Dermoscopy of a skin lesion:
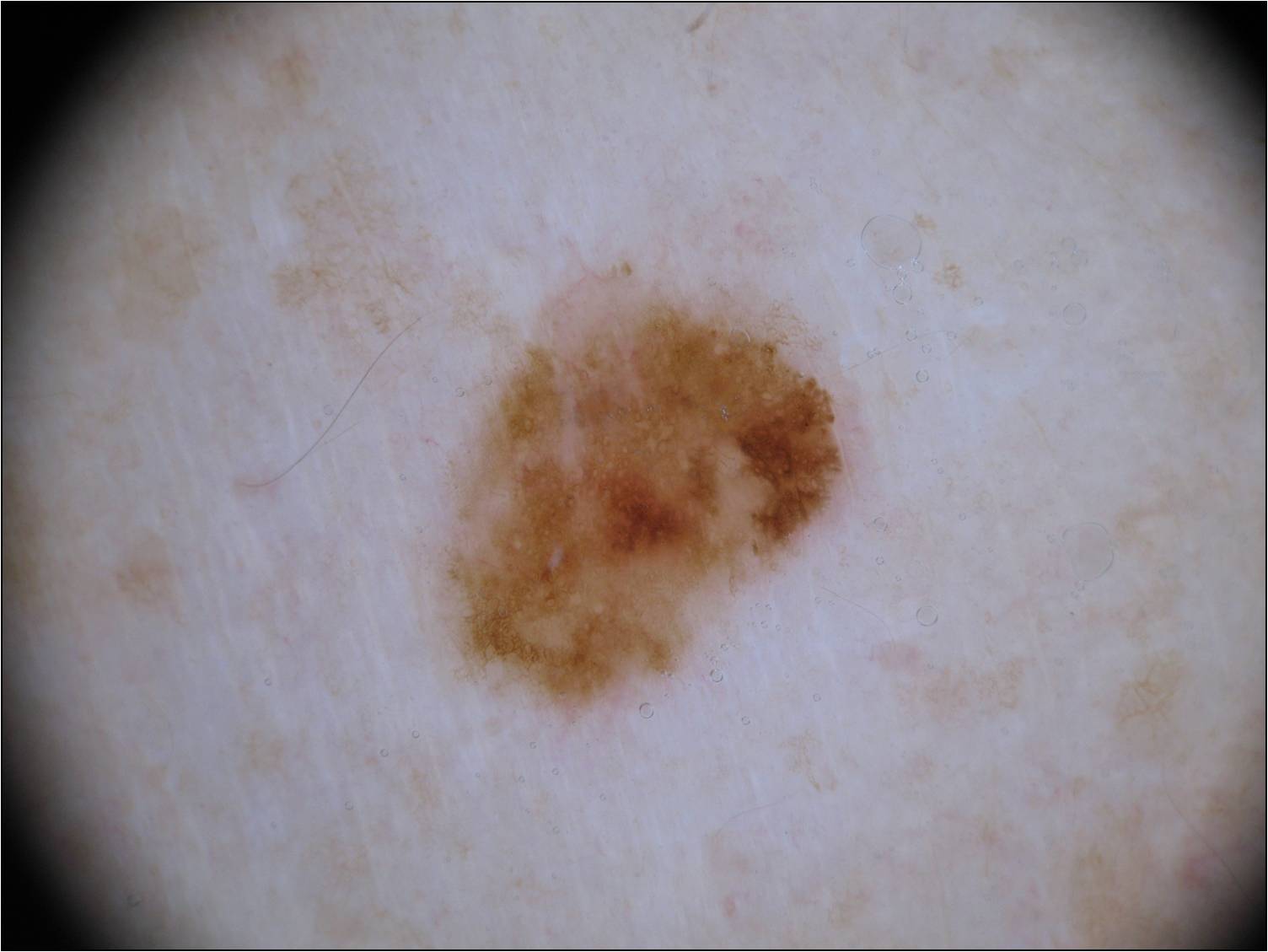Image and clinical context: With coordinates (x1, y1, x2, y2), the lesion occupies the region (428, 258, 857, 726). Conclusion: Histopathology confirmed a melanoma, a malignant skin lesion.